The affected area is the leg · the photo was captured at an angle · female patient, age 18–29 — 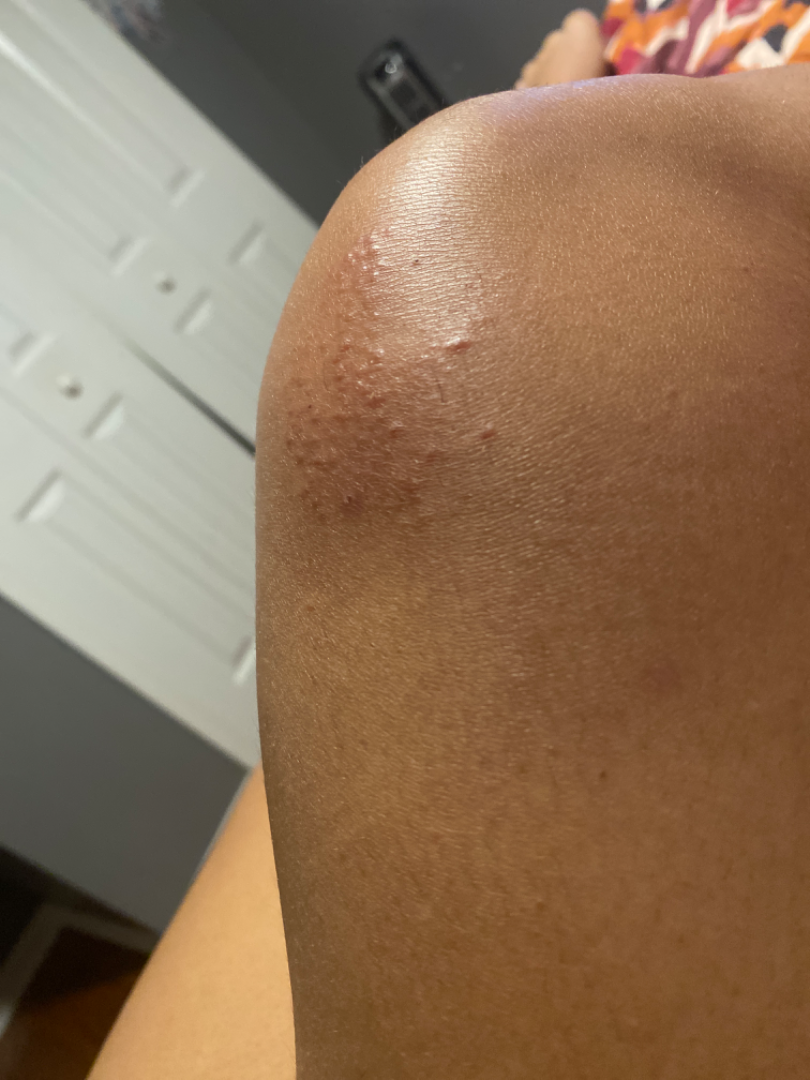lesion texture — flat | diagnostic considerations — favoring Lichen spinulosus; an alternative is Keratosis pilaris; less probable is Lichen nitidus.